This is a dermoscopic photograph of a skin lesion.
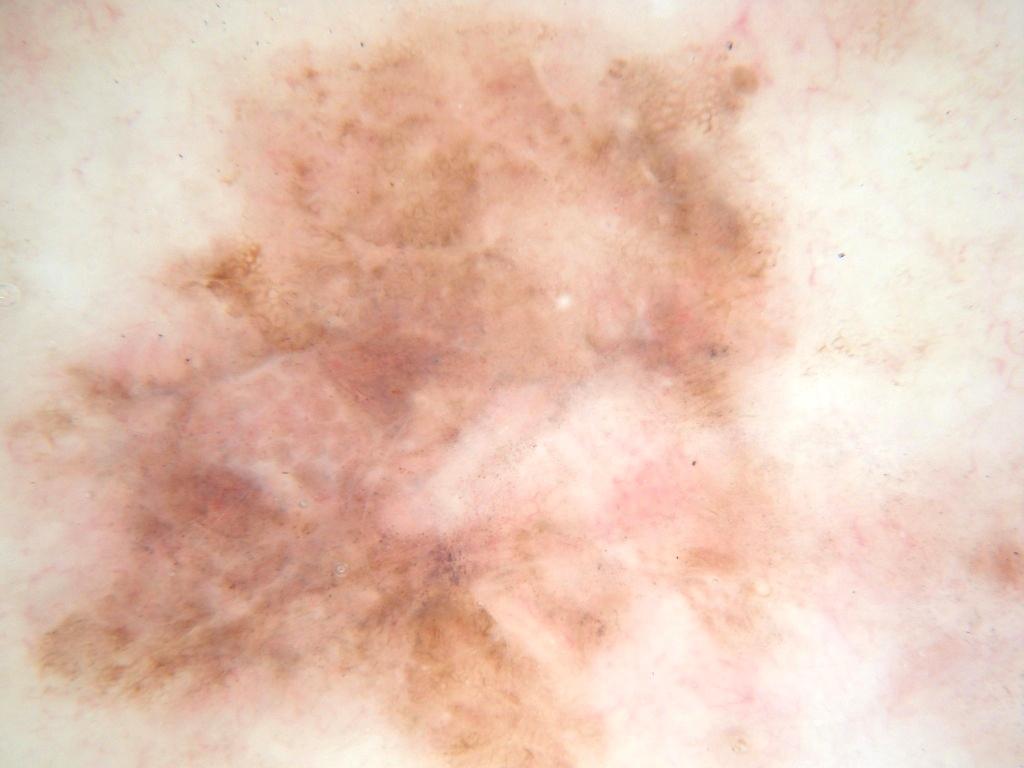lesion bbox = bbox(0, 0, 791, 763) | dermoscopic pattern = globules; absent: streaks | lesion margin = clipped at the frame edge | lesion extent = large | assessment = a malignant skin lesion.